Close-up view.
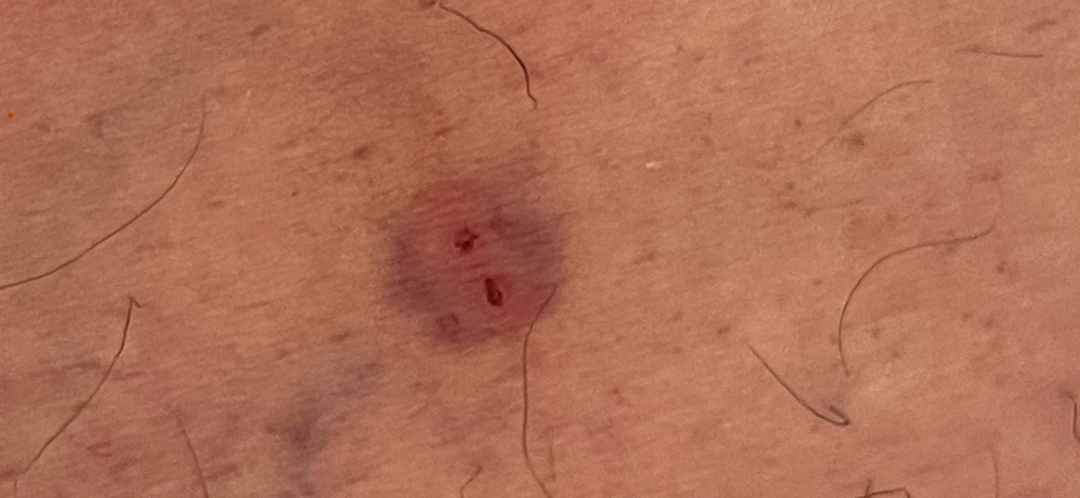Diagnostic features were not clearly distinguishable in this photograph.